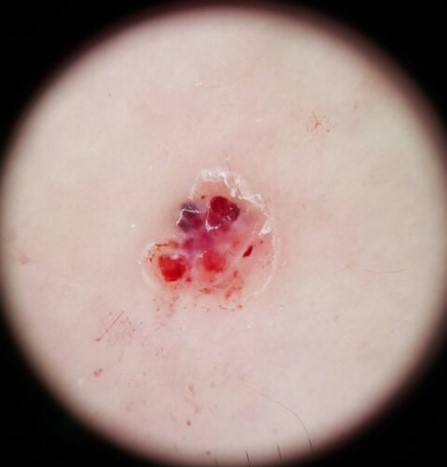Classified as an angiokeratoma.